A close-up photograph. Located on the leg. Female patient, age 50–59: 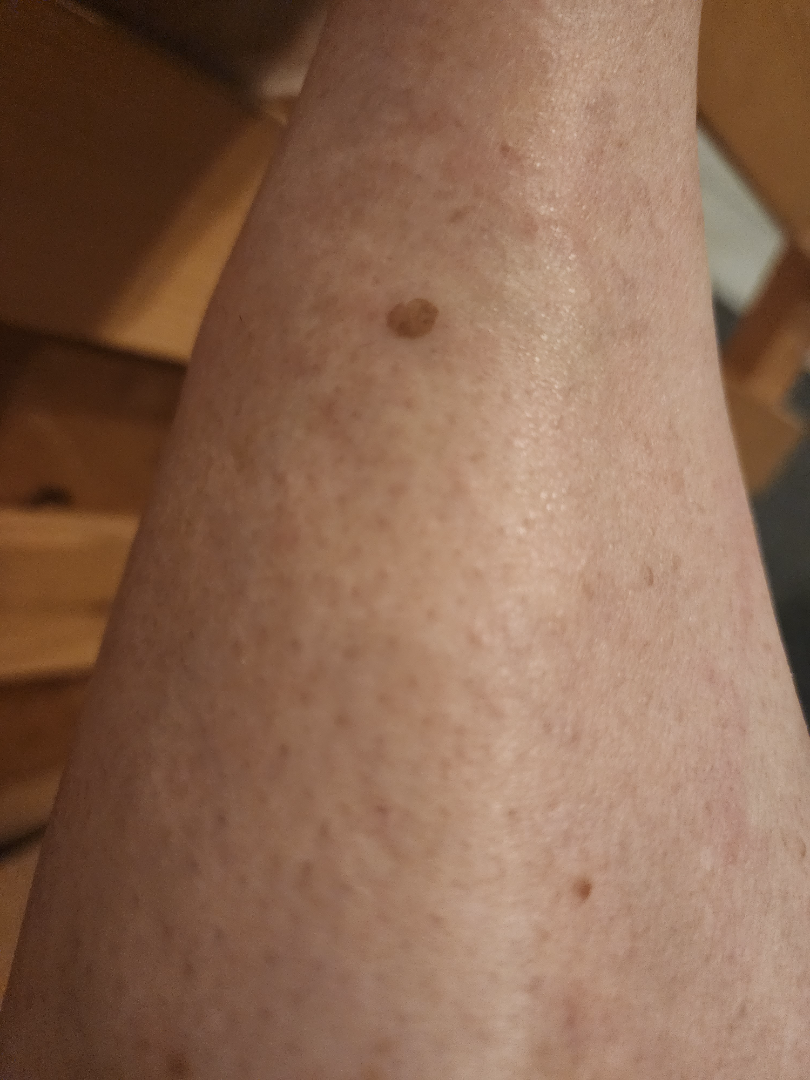The condition could not be reliably identified from the image.
The contributor reports bothersome appearance.
The lesion is described as raised or bumpy and rough or flaky.
The patient reported no systemic symptoms.